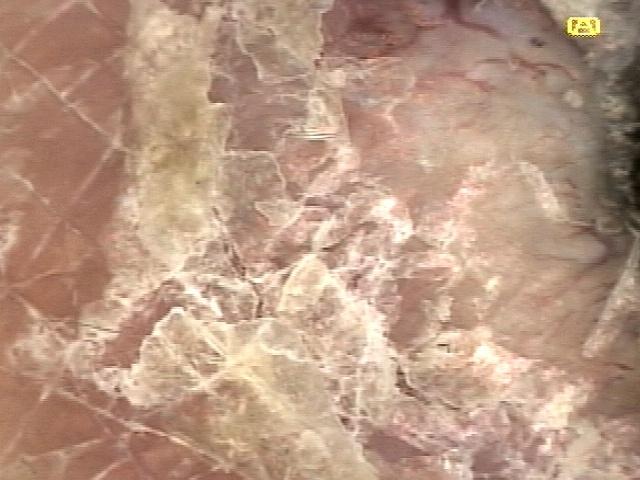Clinical context: A skin lesion imaged with contact-polarized dermoscopy. A female subject roughly 75 years of age. The patient is FST II. The lesion is located on a lower extremity. Conclusion: Histopathology confirmed an epidermal proliferation — a squamous cell carcinoma.